The patient reports itching, burning and pain · close-up view · the palm is involved · reported duration is about one day — 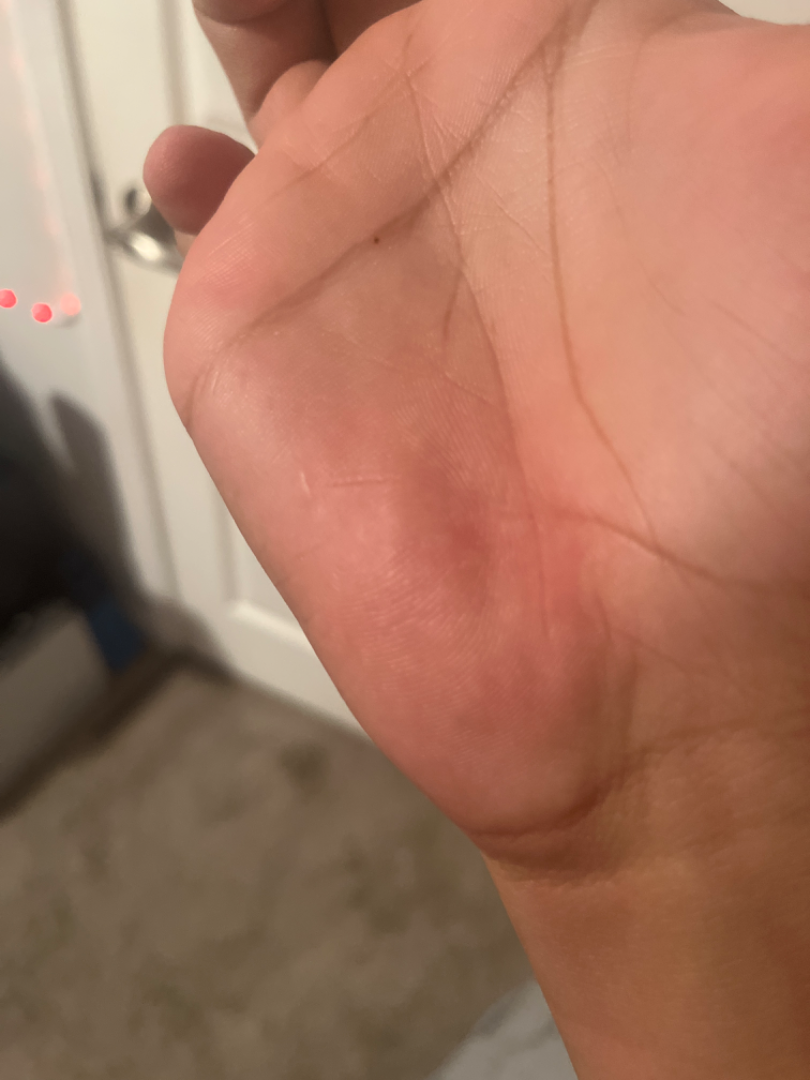The case was difficult to assess from the available photograph.